The photograph is a close-up of the affected area; the patient described the issue as a rash; the lesion involves the leg, front of the torso and back of the torso; the lesion is described as rough or flaky; no relevant lesion symptoms reported: 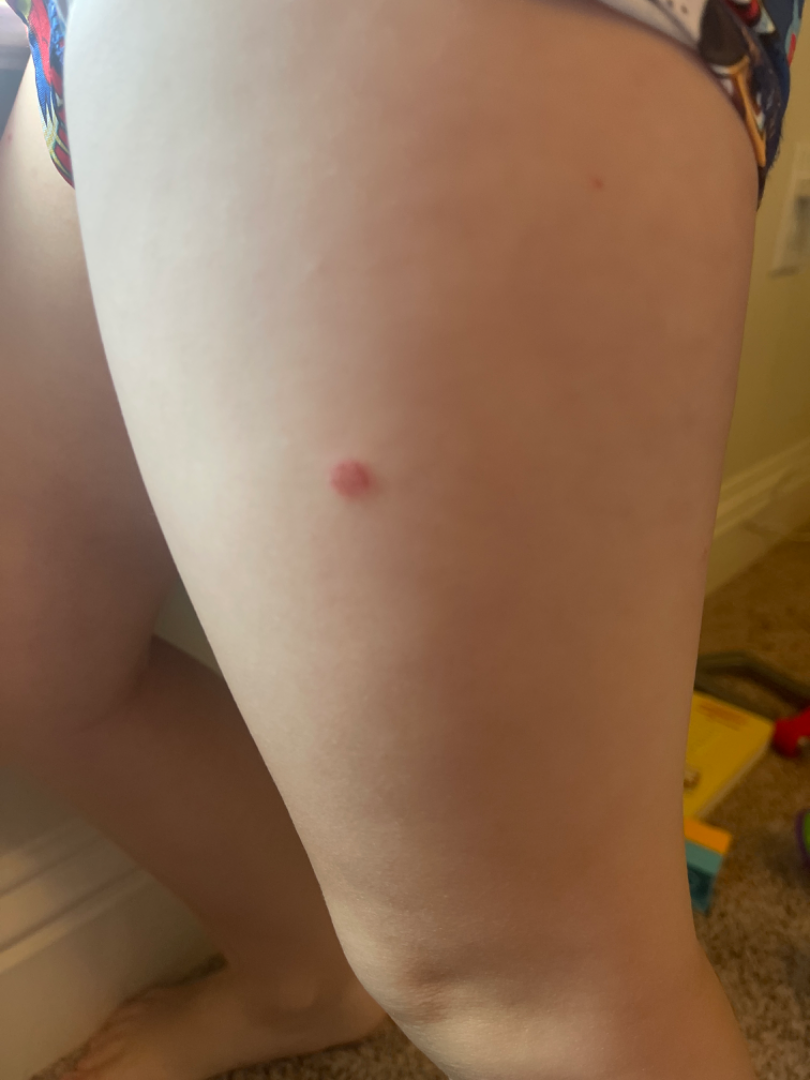Review: Single-reviewer assessment: Hemangioma, Melanocytic Nevus and Pyogenic granuloma were each considered, in no particular order.